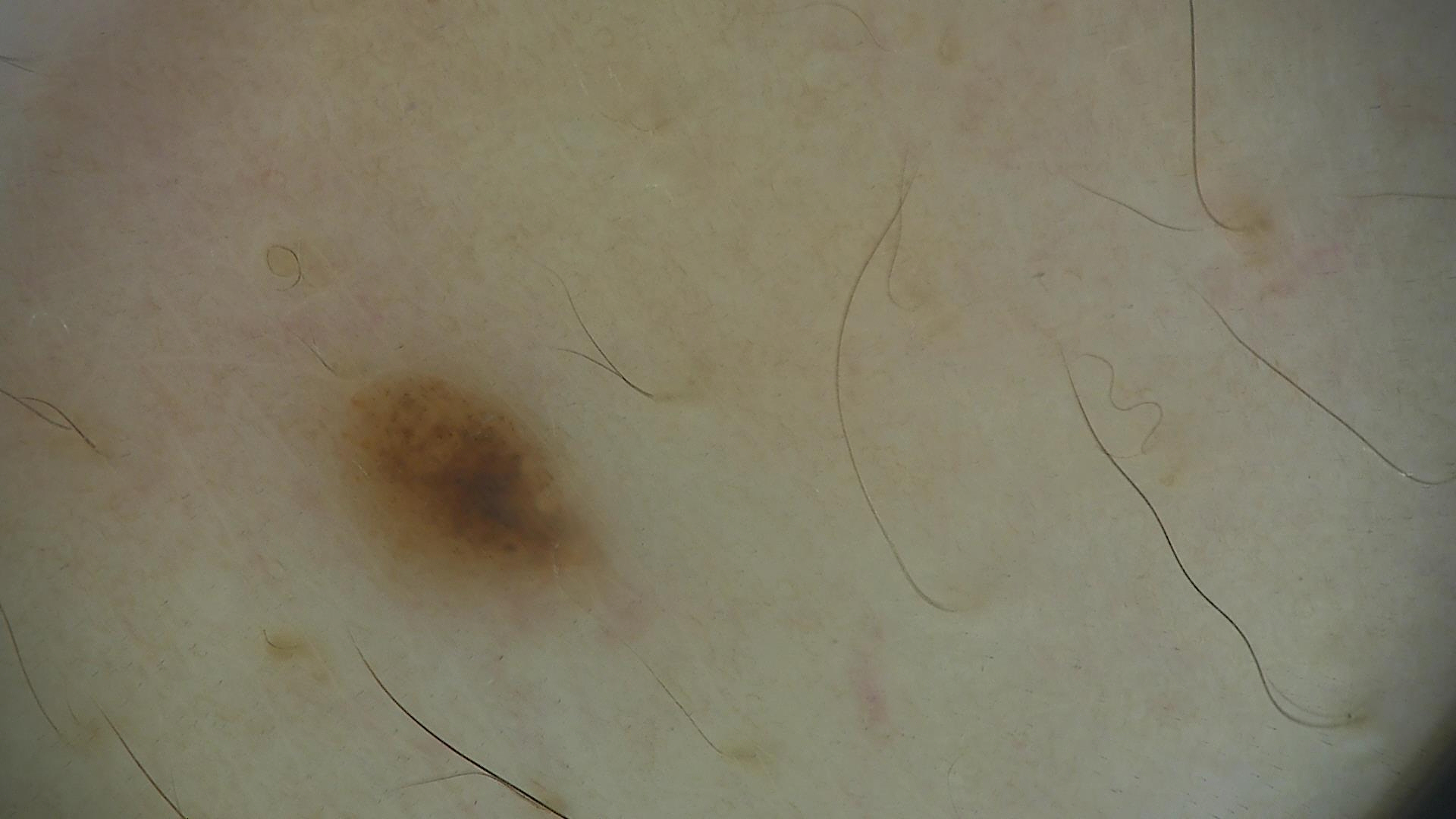Labeled as a dysplastic junctional nevus.